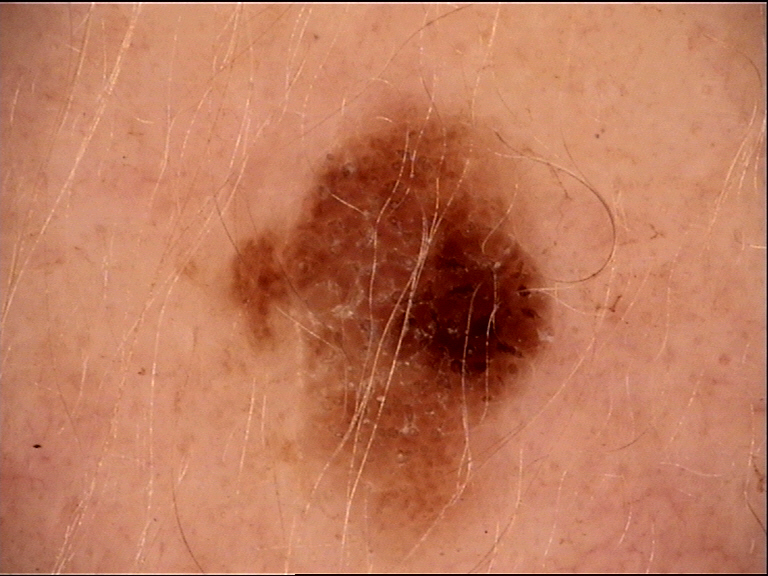Q: What was the diagnostic impression?
A: dysplastic compound nevus (expert consensus)